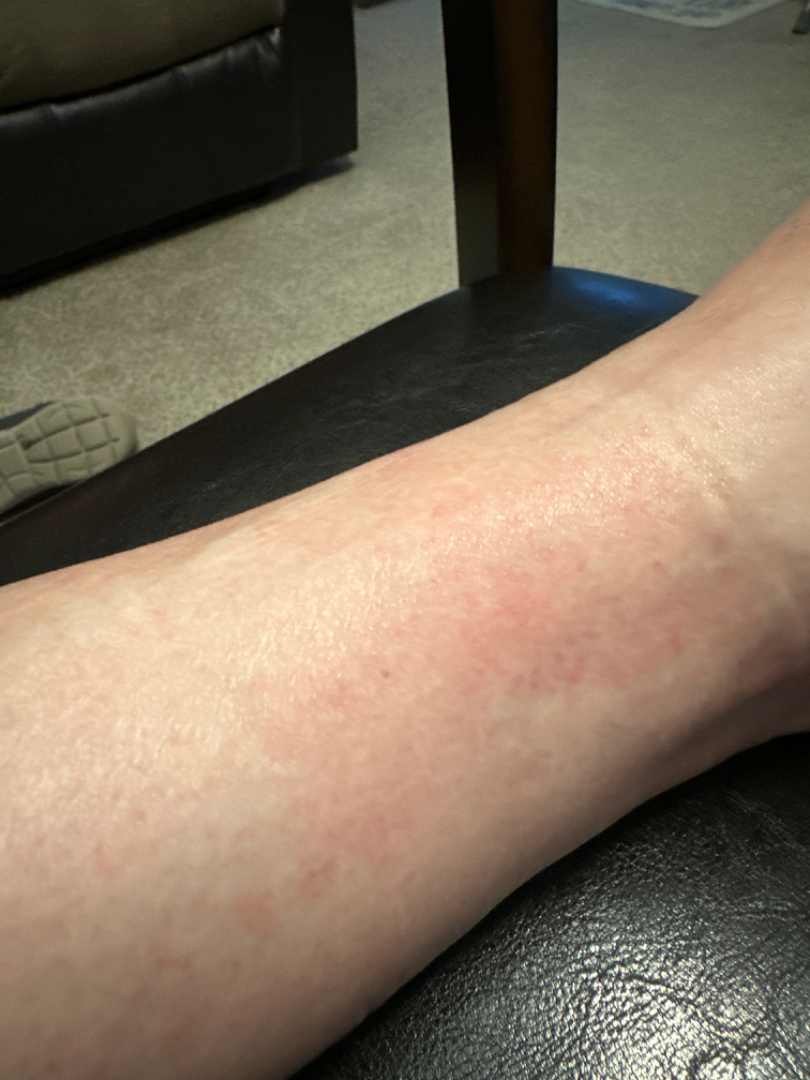Notes:
– assessment — indeterminate